A dermoscopy image of a single skin lesion.
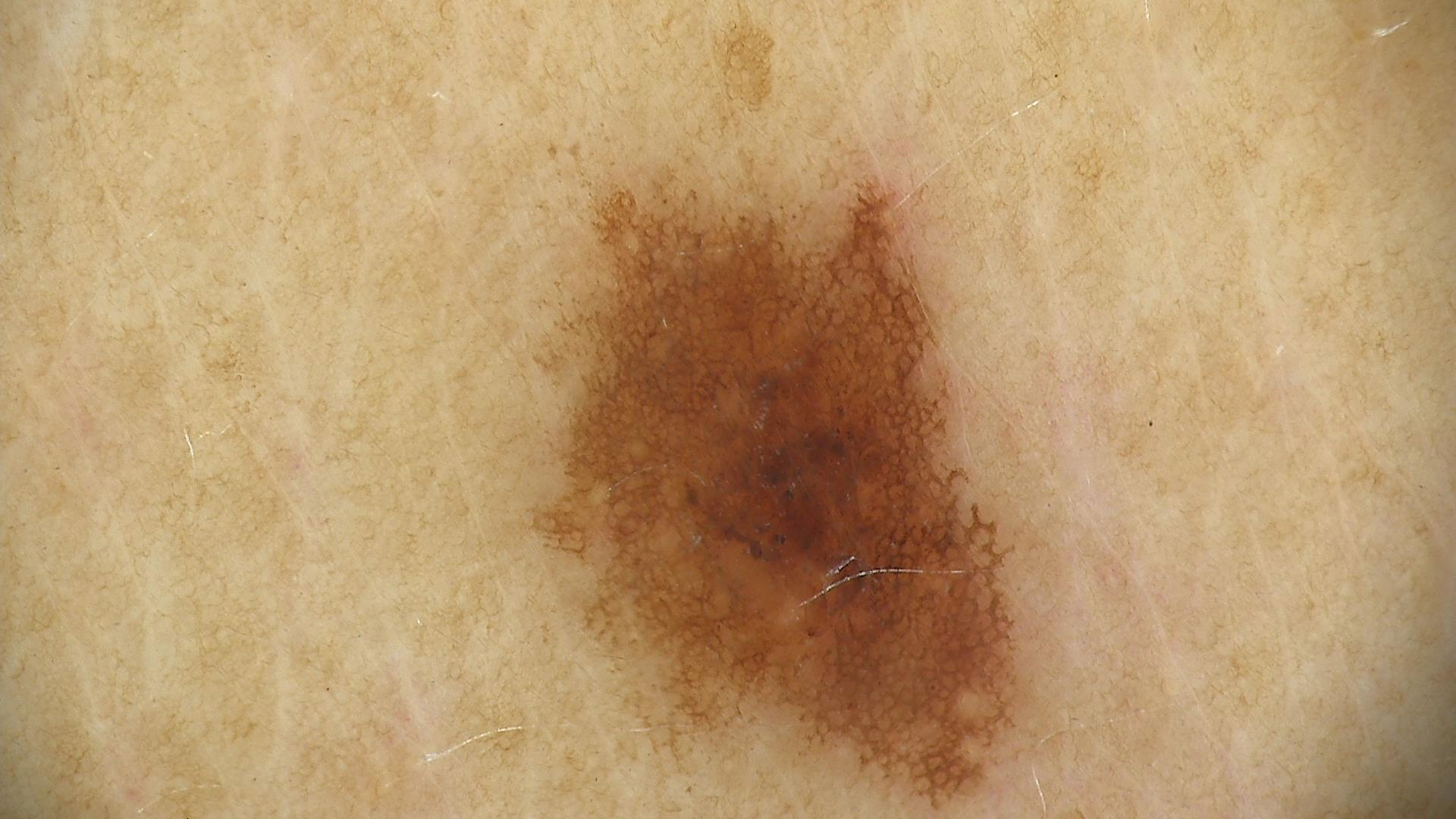The diagnosis was a benign lesion — a dysplastic junctional nevus.